The contributor reports pain, itching and burning. The condition has been present for one to four weeks. The affected area is the top or side of the foot. An image taken at a distance. The contributor reports the lesion is raised or bumpy and rough or flaky. No constitutional symptoms were reported.
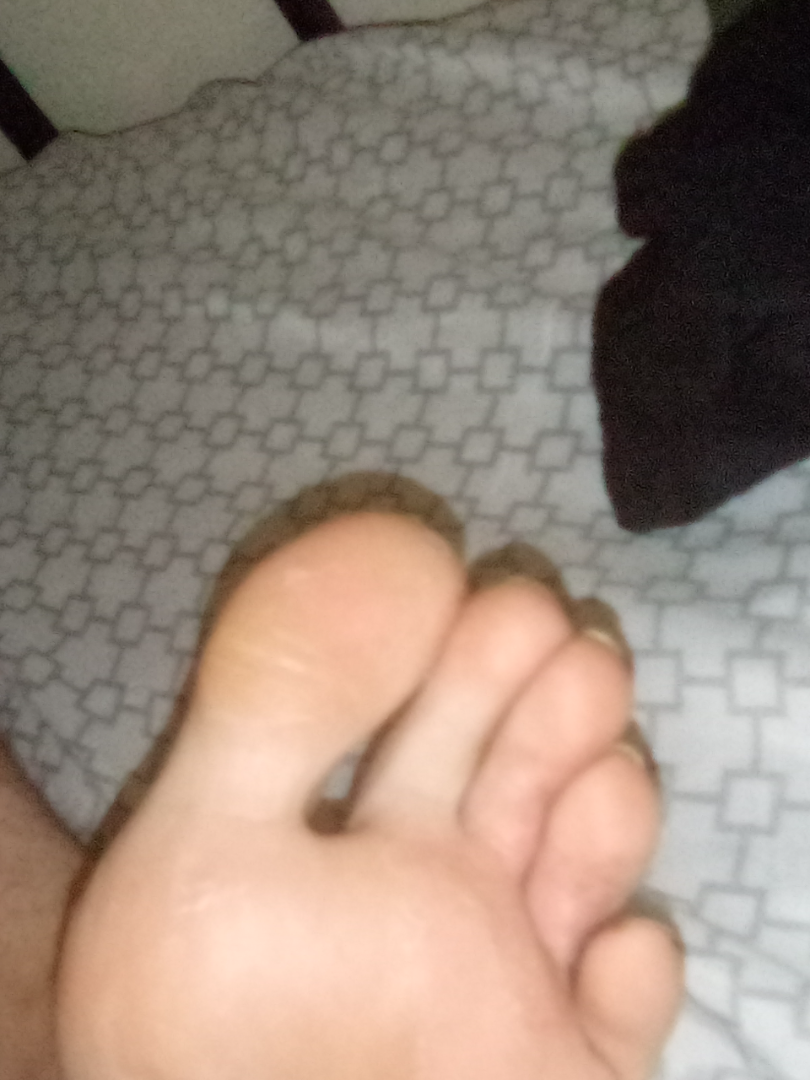Assessment:
Most likely Tinea; also consider Chilblain; an alternative is Eczema.